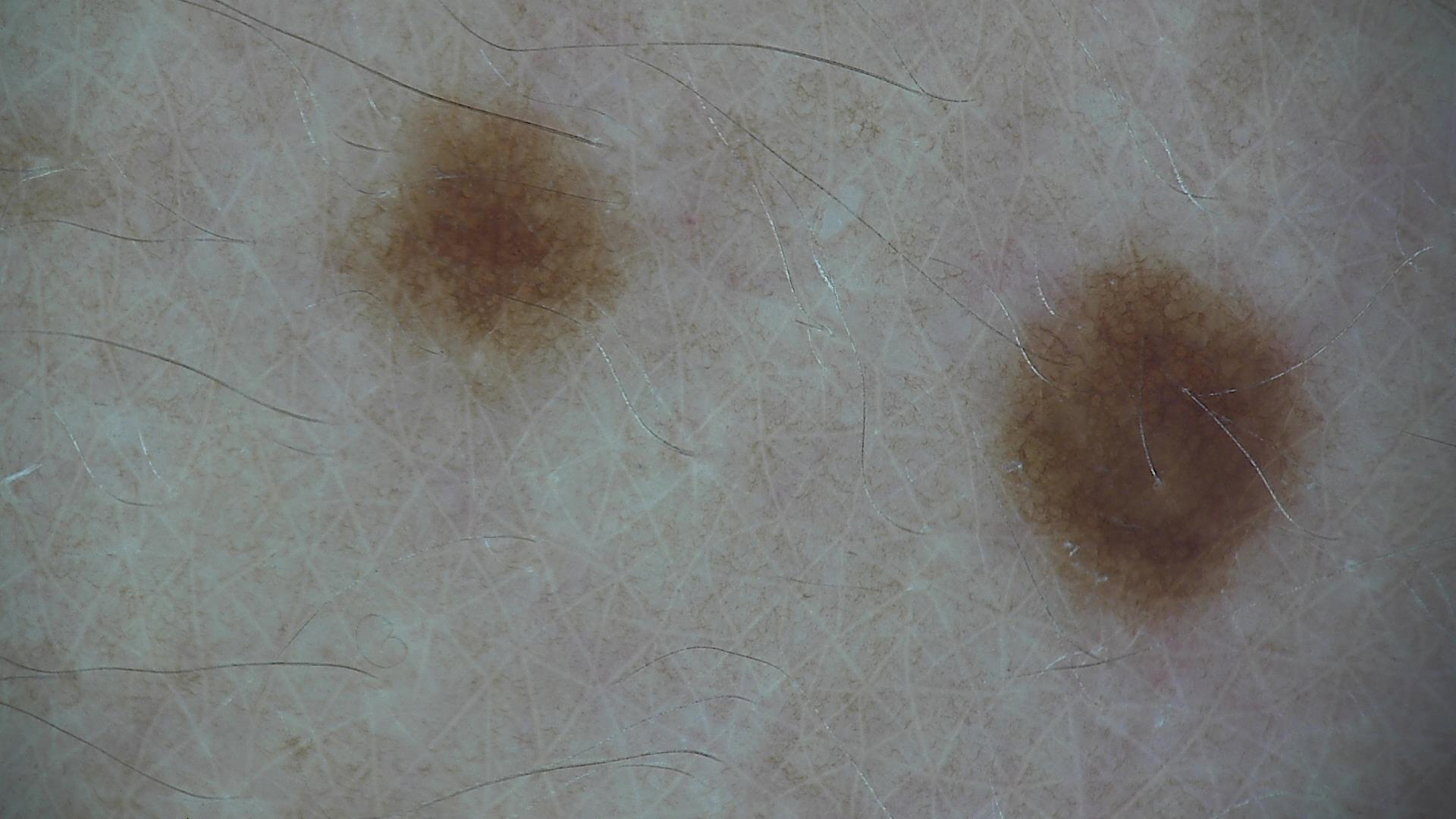Q: What is the imaging modality?
A: dermatoscopy
Q: What is this lesion?
A: dysplastic junctional nevus (expert consensus)